Dermoscopy of a skin lesion:
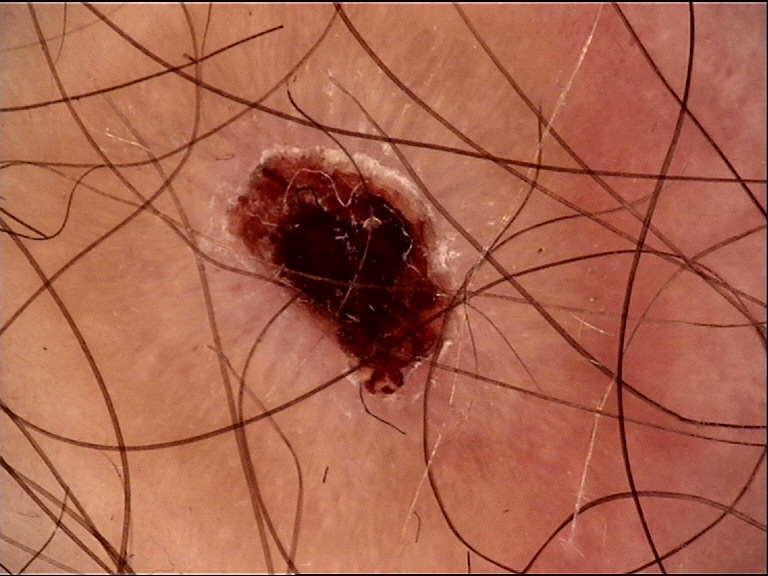{
  "diagnosis": {
    "name": "dermatofibroma",
    "code": "df",
    "malignancy": "benign",
    "super_class": "non-melanocytic",
    "confirmation": "expert consensus"
  }
}